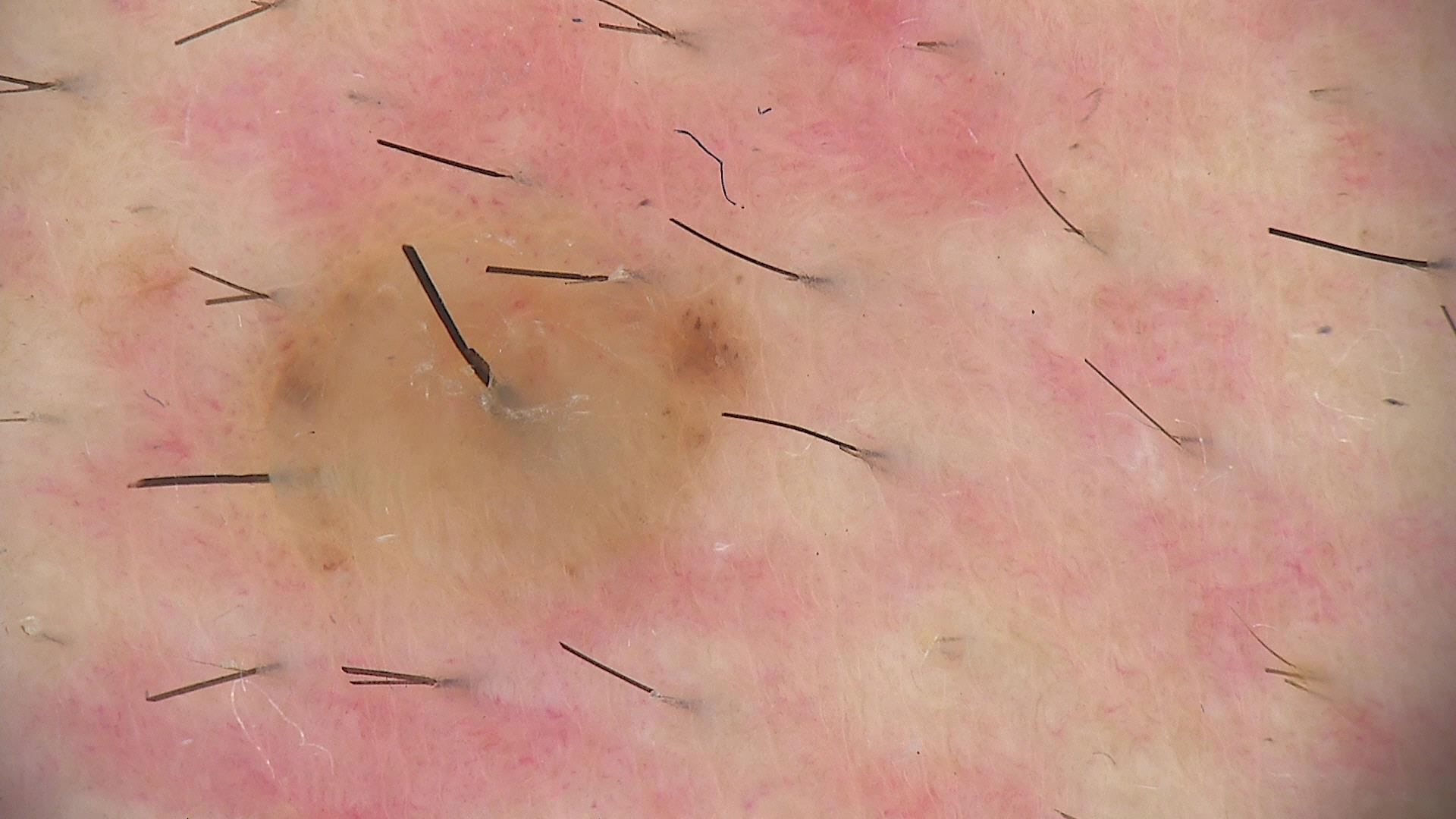The diagnosis was a banal lesion — a dermal nevus.